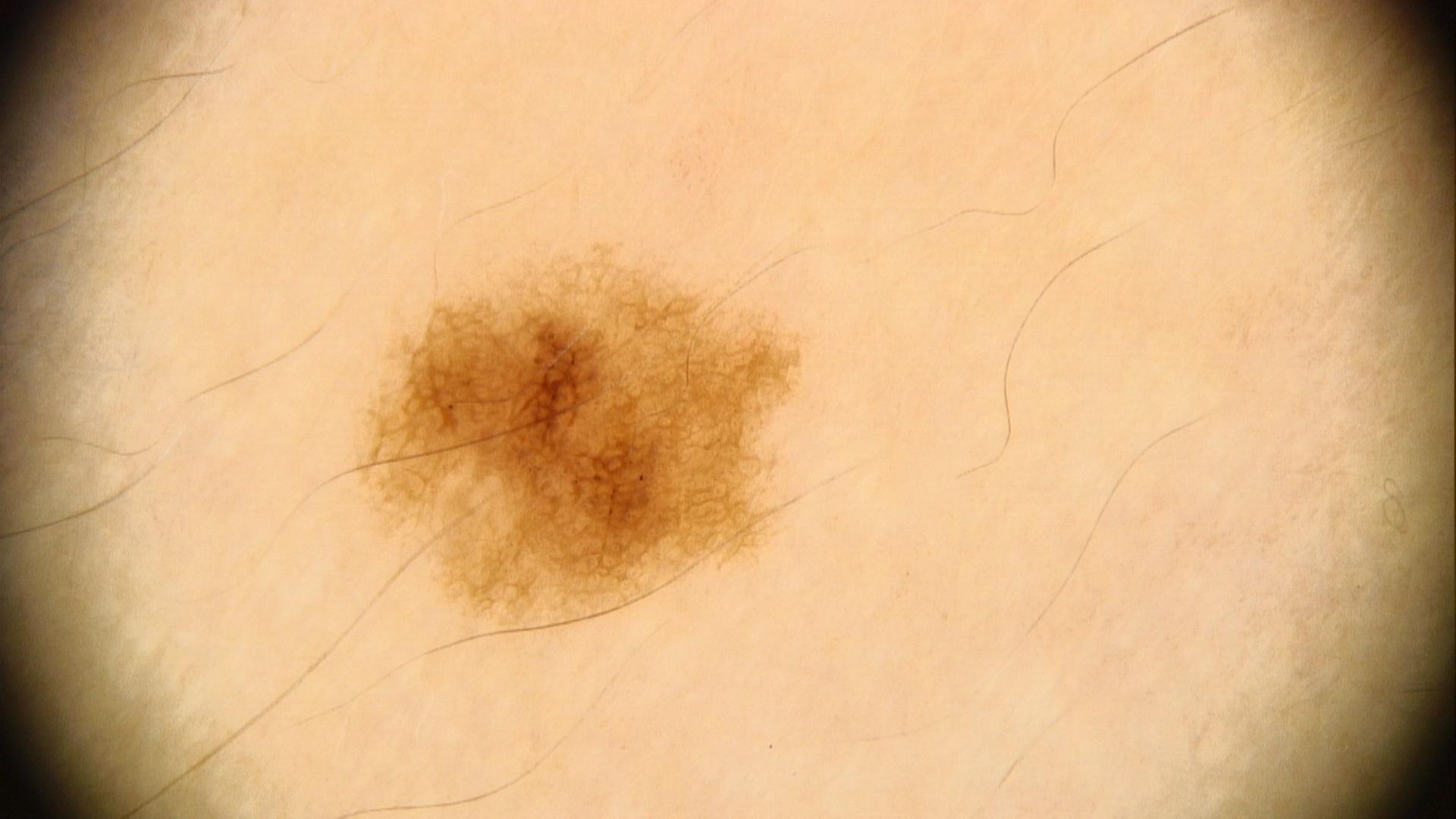Q: What is the imaging modality?
A: contact-polarized dermoscopy
Q: What are the patient's age and sex?
A: female, aged 18 to 22
Q: Where is the lesion located?
A: a lower extremity
Q: What was the clinical impression?
A: Nevus